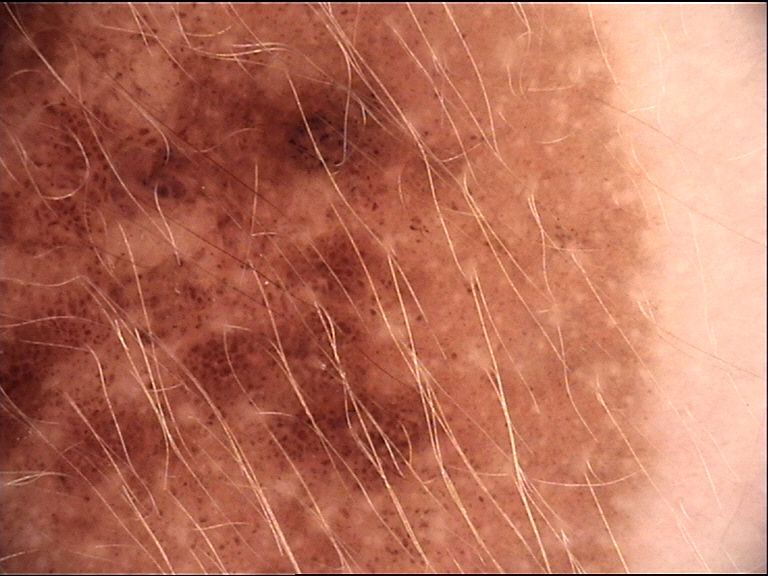Findings:
Dermoscopy of a skin lesion. The architecture is that of a banal lesion.
Impression:
Diagnosed as a congenital junctional nevus.